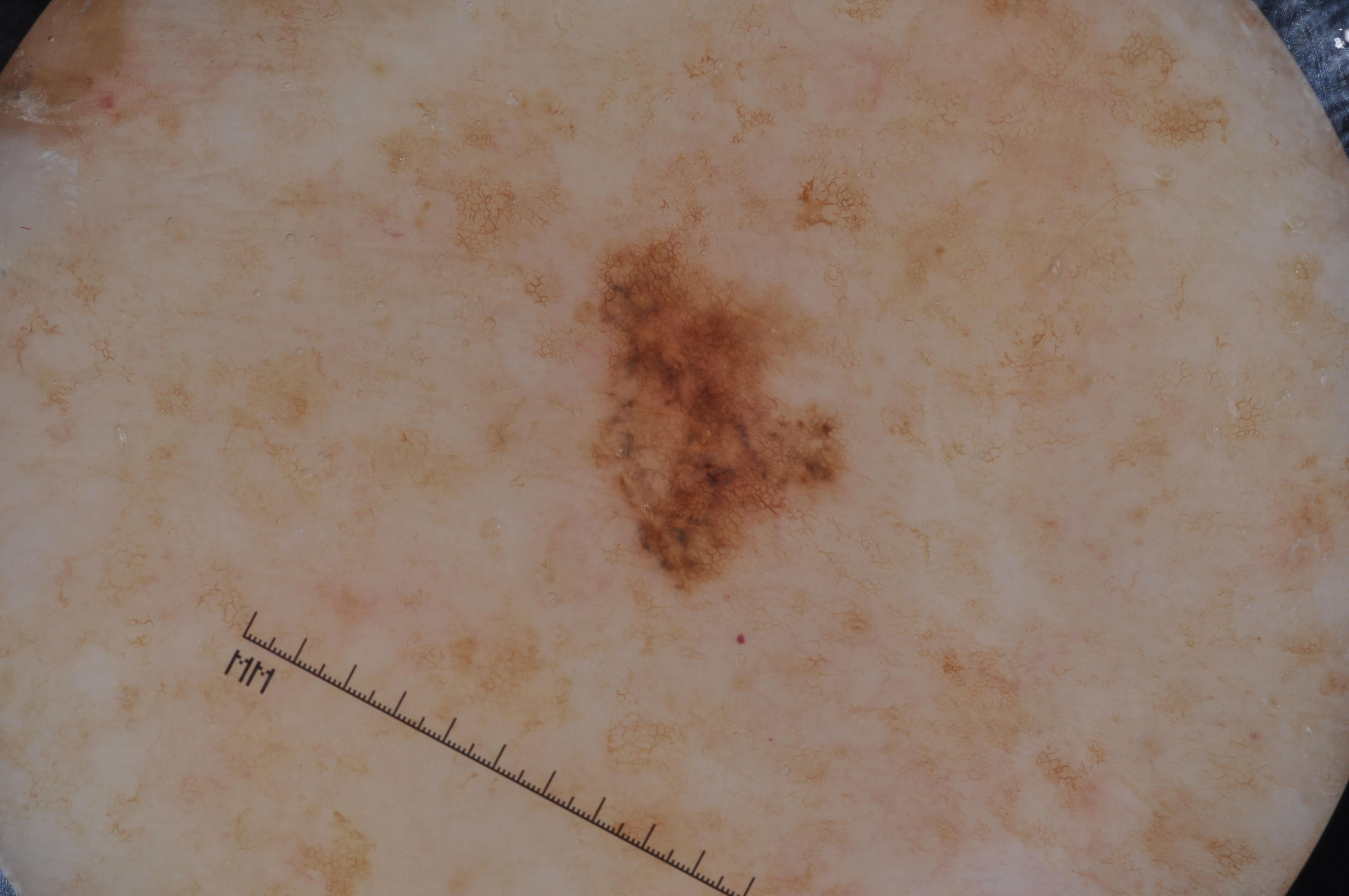A dermoscopy image of a single skin lesion. With coordinates (x1, y1, x2, y2), the lesion spans [590, 245, 843, 581]. Dermoscopic review identifies pigment network; no milia-like cysts, streaks, or negative network. A small lesion within a wider field of skin. Histopathology confirmed a melanoma.